The patient says their skin reddens with sun exposure; acquired for a research image collection, with no referral diagnosis; by self-report, a family history of skin cancer, a personal history of cancer, a personal history of skin cancer, and no prior organ transplant; a female subject aged 54; a clinical close-up of a skin lesion:
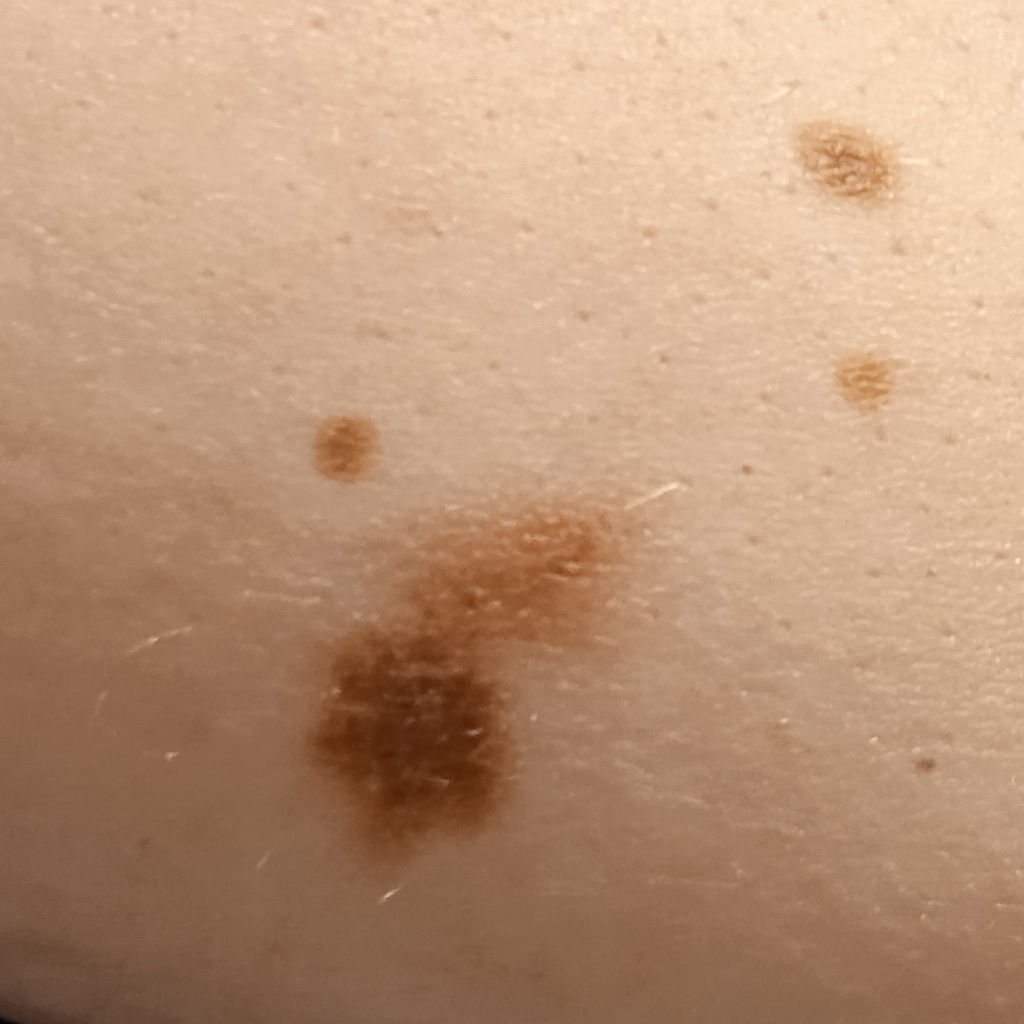Summary:
The lesion is on the torso. The lesion measures approximately 17.5 mm.
Conclusion:
The lesion was assessed as a melanoma.